An image taken at an angle, the affected area is the top or side of the foot and arm, the contributor is male.
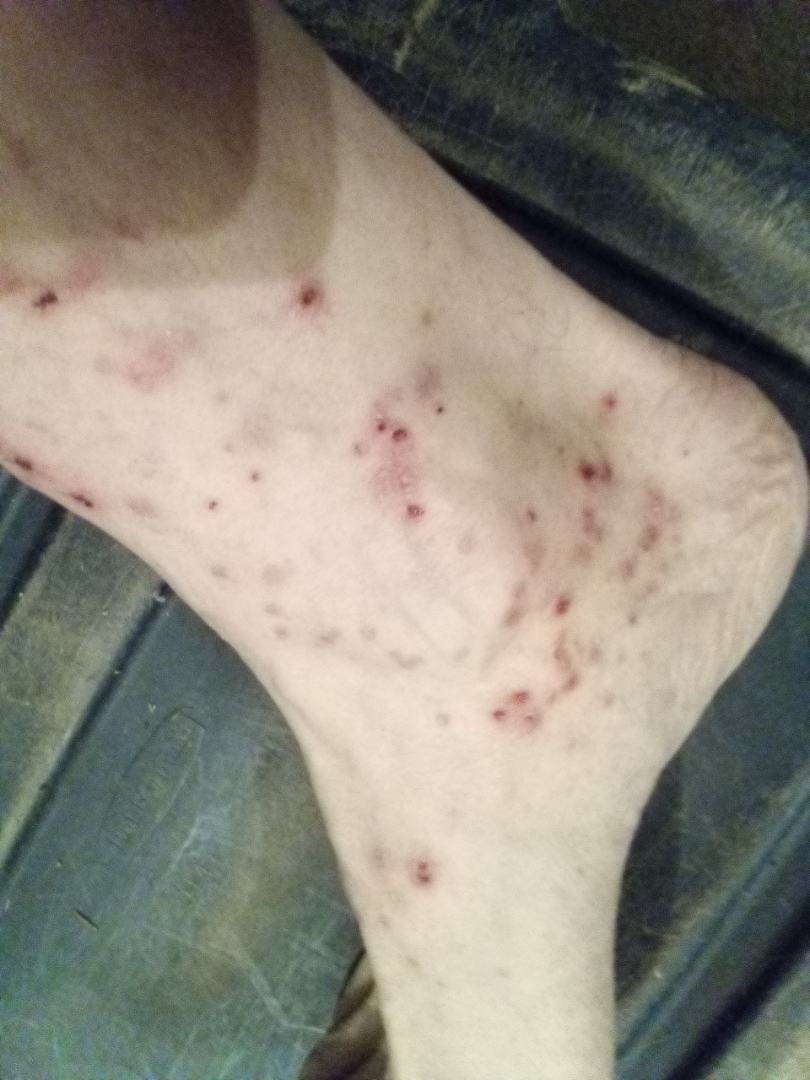impression — Insect Bite (0.50); Eczema (0.50).